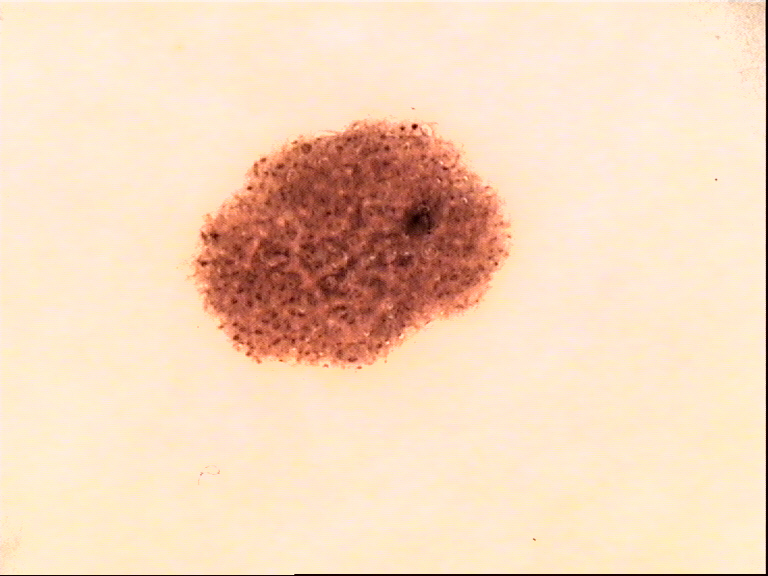A dermoscopic close-up of a skin lesion. The diagnostic label was a dysplastic junctional nevus.